A dermoscopic image of a skin lesion.
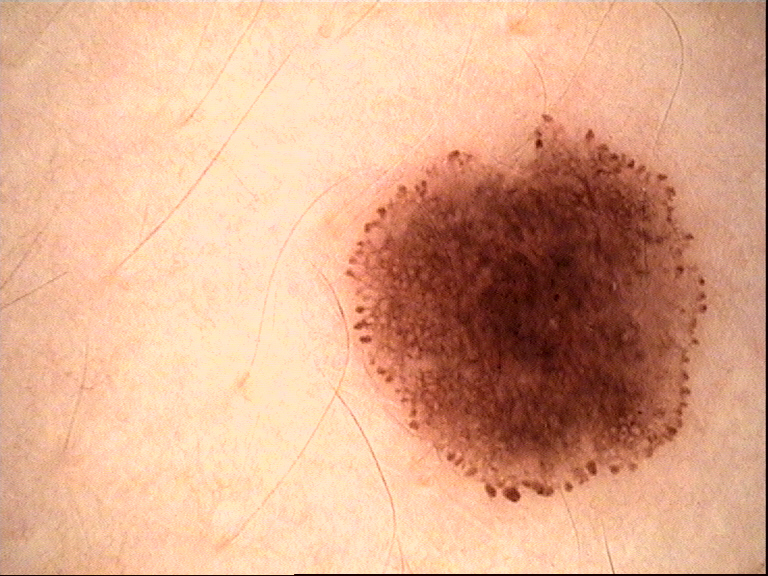Conclusion: Classified as a dysplastic junctional nevus.